A dermatoscopic image of a skin lesion:
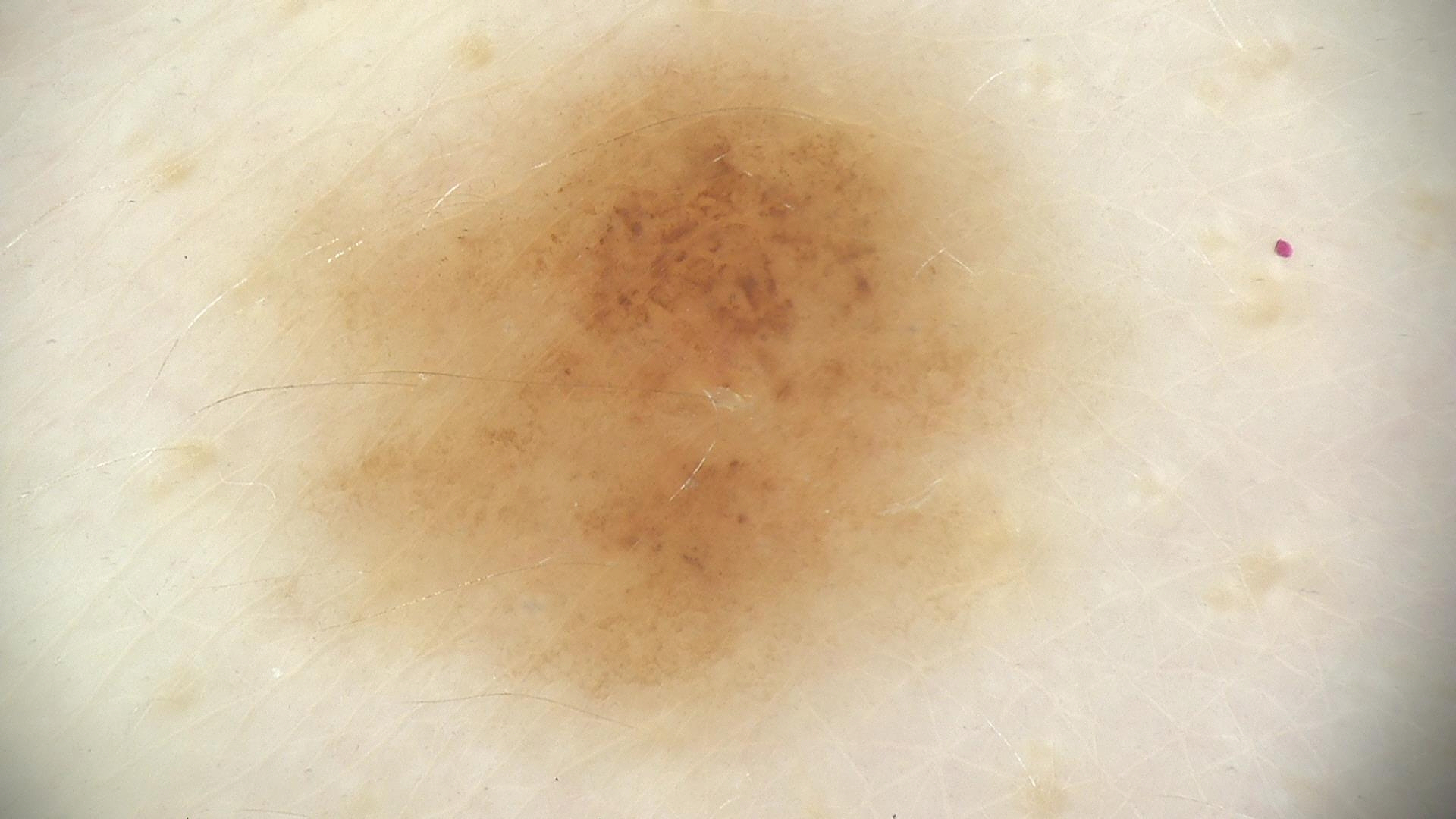diagnosis:
  name: dysplastic junctional nevus
  code: jd
  malignancy: benign
  super_class: melanocytic
  confirmation: expert consensus